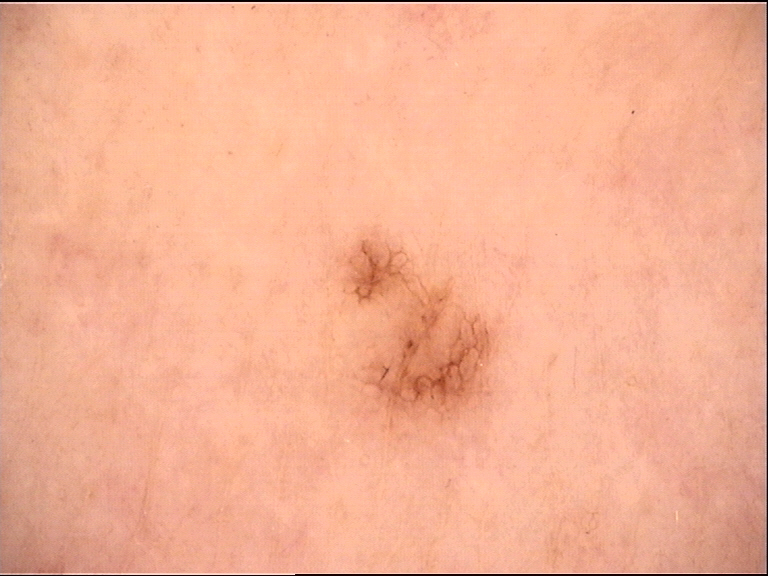Classified as a dysplastic junctional nevus.